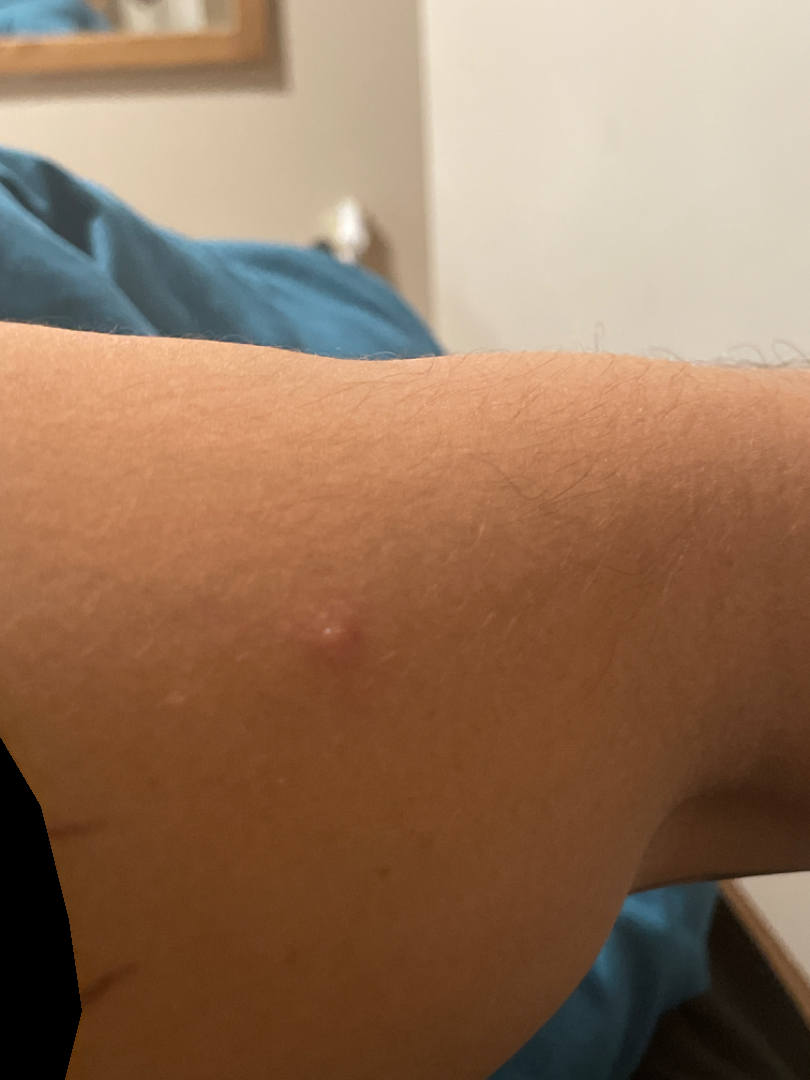body site — arm
view — at a distance
differential — the impression was split between Impetigo, Insect Bite and Allergic Contact Dermatitis